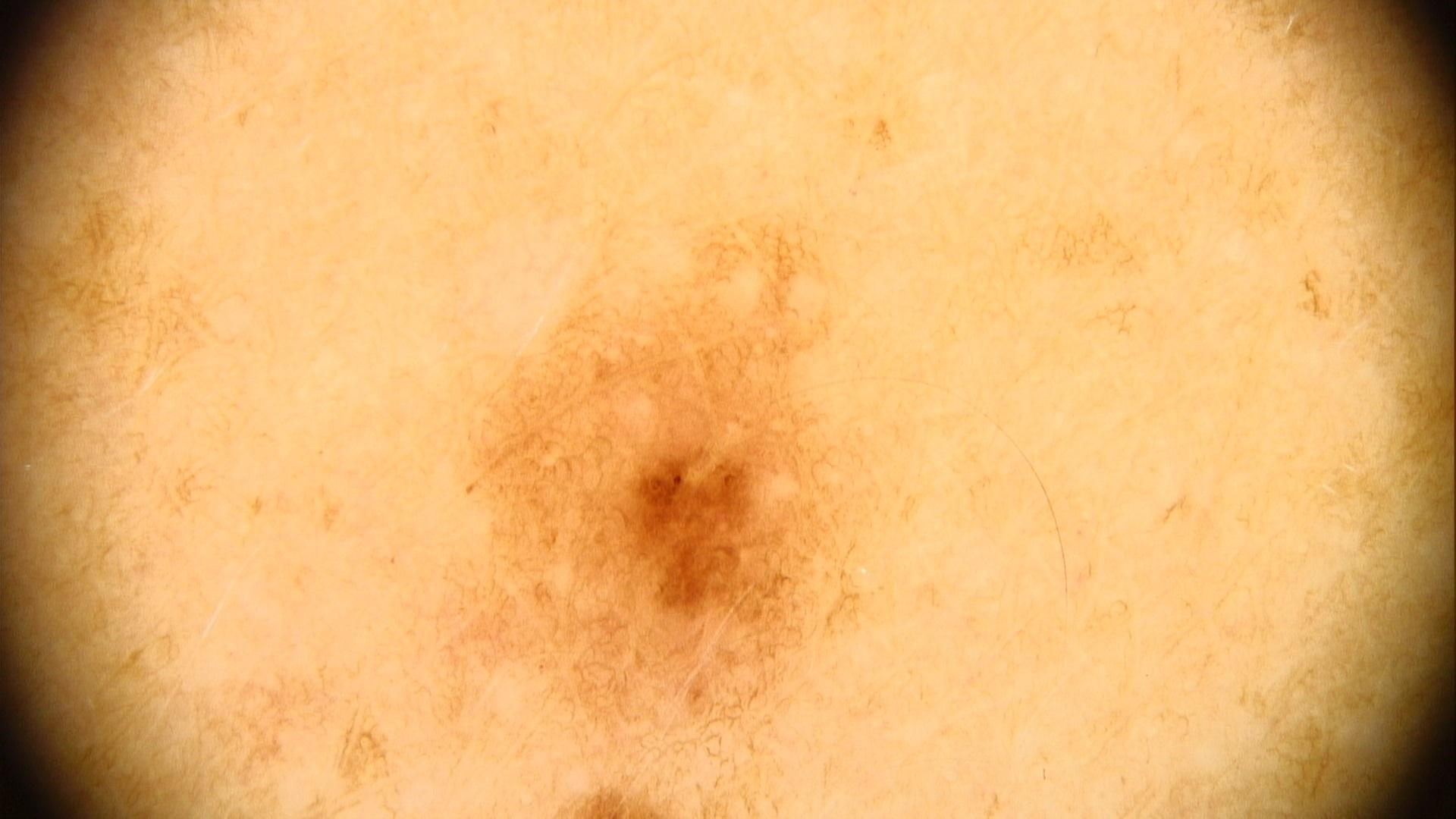• subject — male, aged 38-42
• modality — dermoscopic image
• location — the trunk (the posterior trunk)
• impression — Nevus